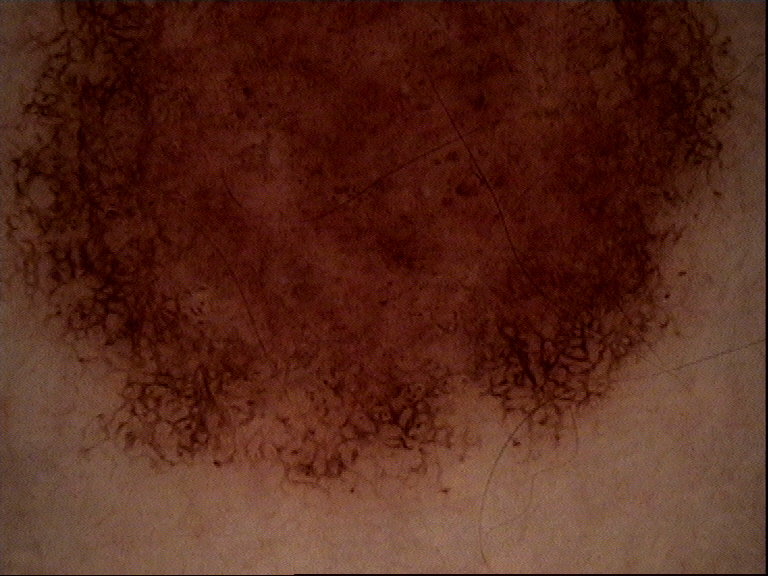– diagnosis · congenital dysplastic compound nevus (expert consensus)